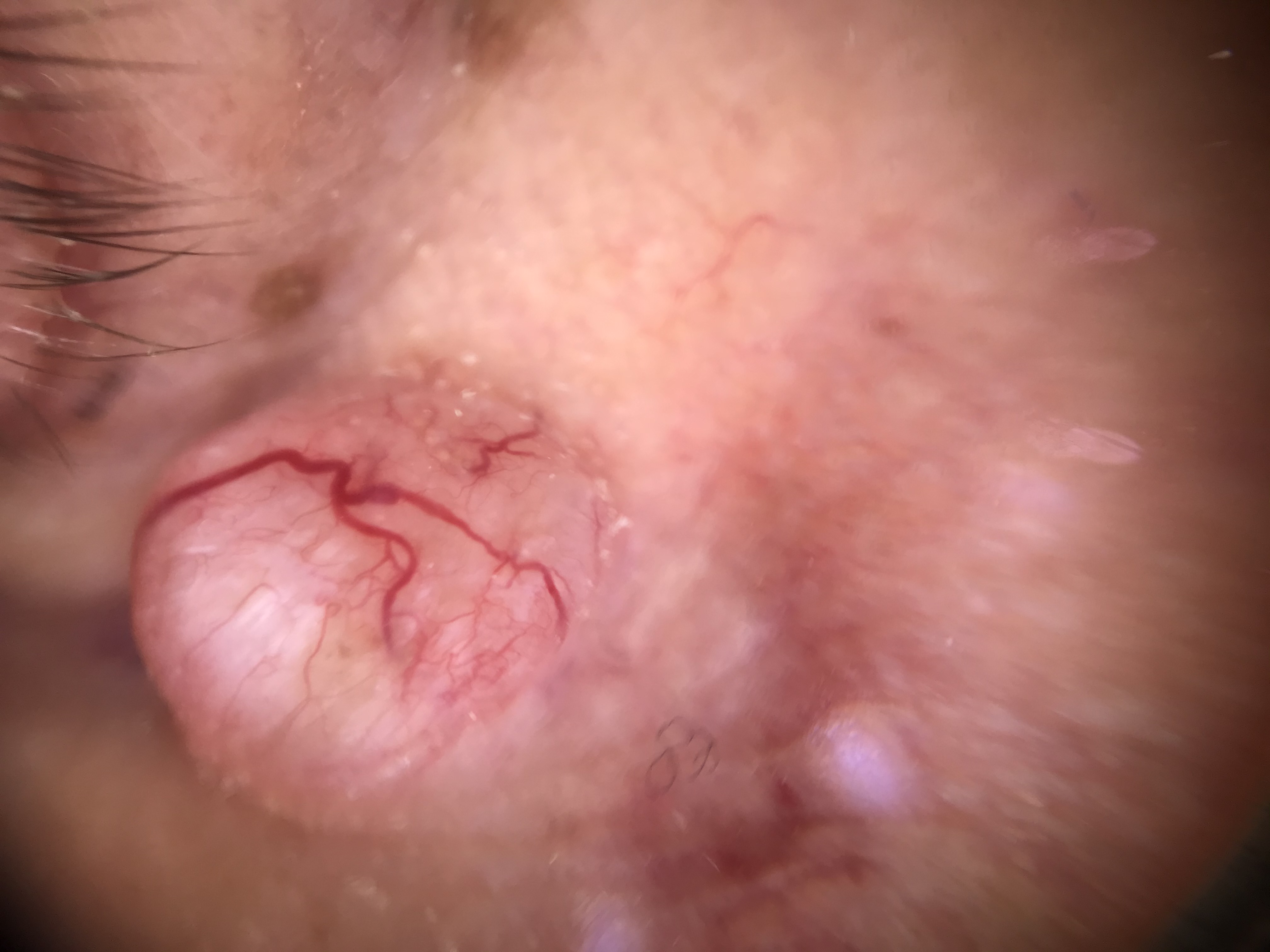Q: What is the lesion category?
A: keratinocytic
Q: What did the workup show?
A: basal cell carcinoma (biopsy-proven)